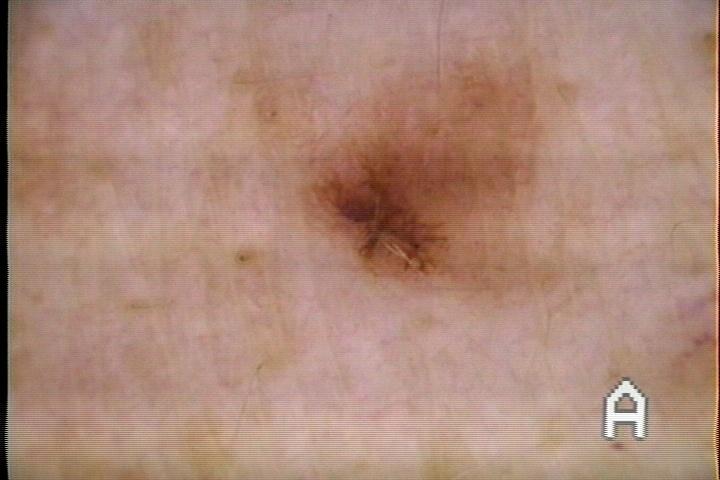Case:
• patient · male, approximately 70 years of age
• modality · contact-polarized dermoscopy
• location · the trunk (the posterior trunk)
• diagnostic label · Nevus (biopsy-proven)